A dermoscopy image of a single skin lesion.
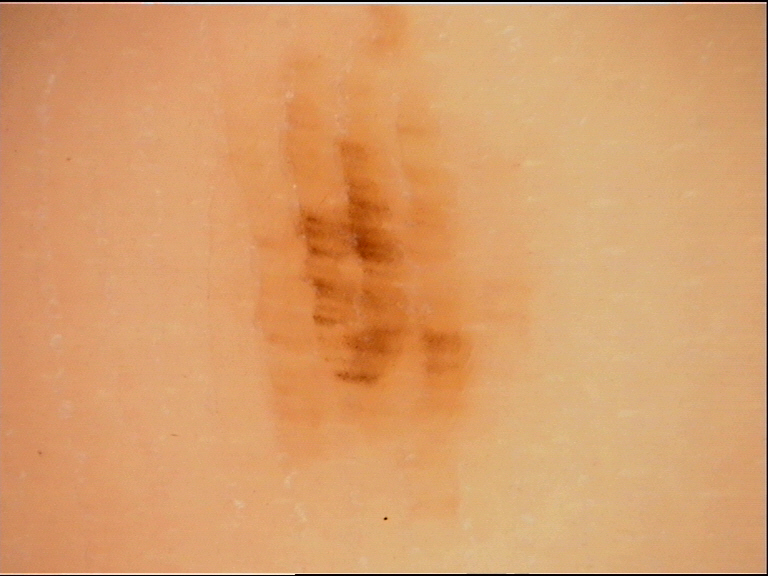Findings:
This is a banal lesion.
Impression:
The diagnostic label was an acral junctional nevus.